The chart notes prior skin cancer (patient or family) and pesticide exposure · Fitzpatrick phototype II · a female patient 63 years of age · a clinical close-up photograph of a skin lesion: 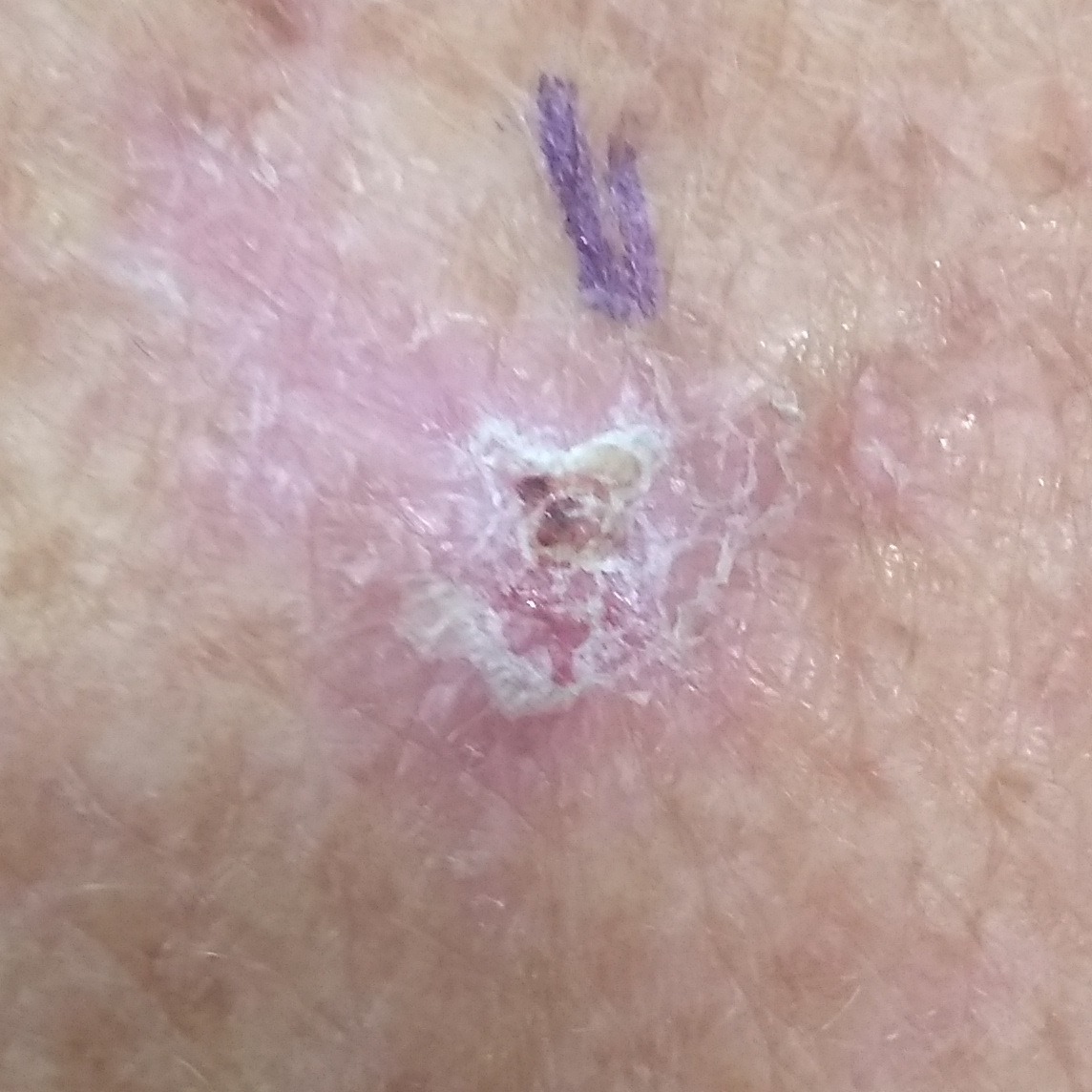  lesion_location: an arm
  lesion_size:
    diameter_1_mm: 19.0
    diameter_2_mm: 12.0
  symptoms:
    present:
      - growth
      - itching
    absent:
      - bleeding
  diagnosis:
    name: actinic keratosis
    code: ACK
    malignancy: indeterminate
    confirmation: histopathology